The contributor is a female aged 18–29; this is a close-up image:
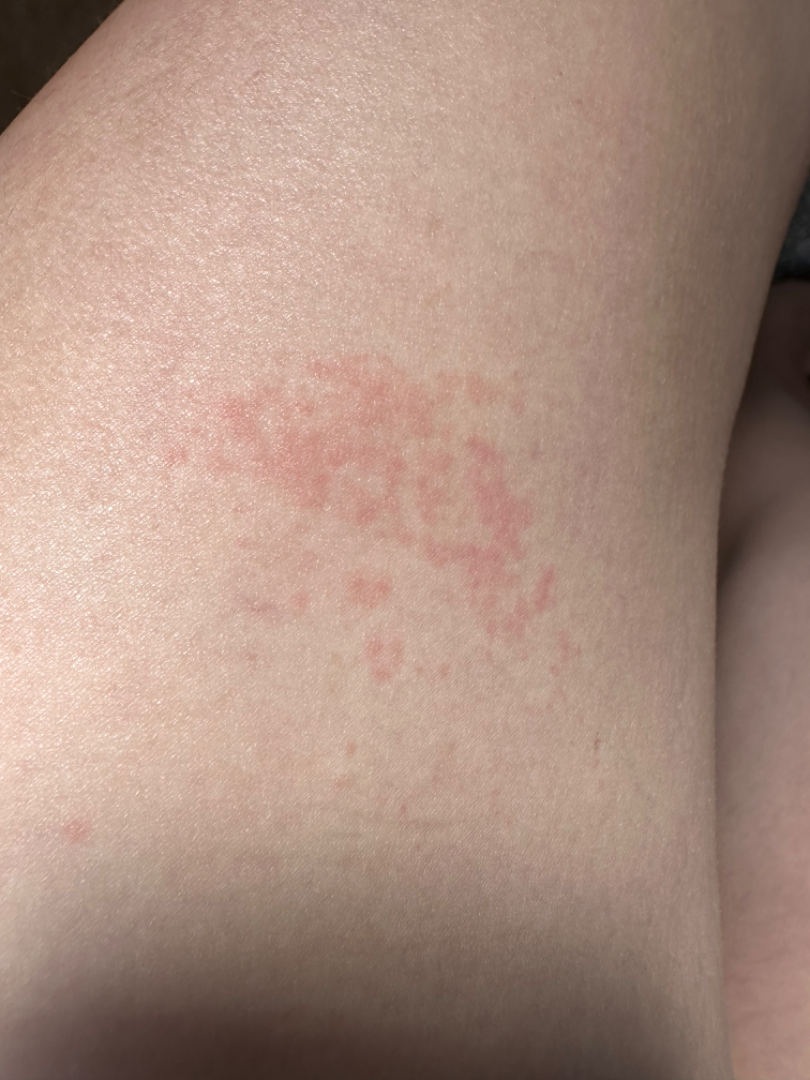Findings:
– assessment — indeterminate from the photograph